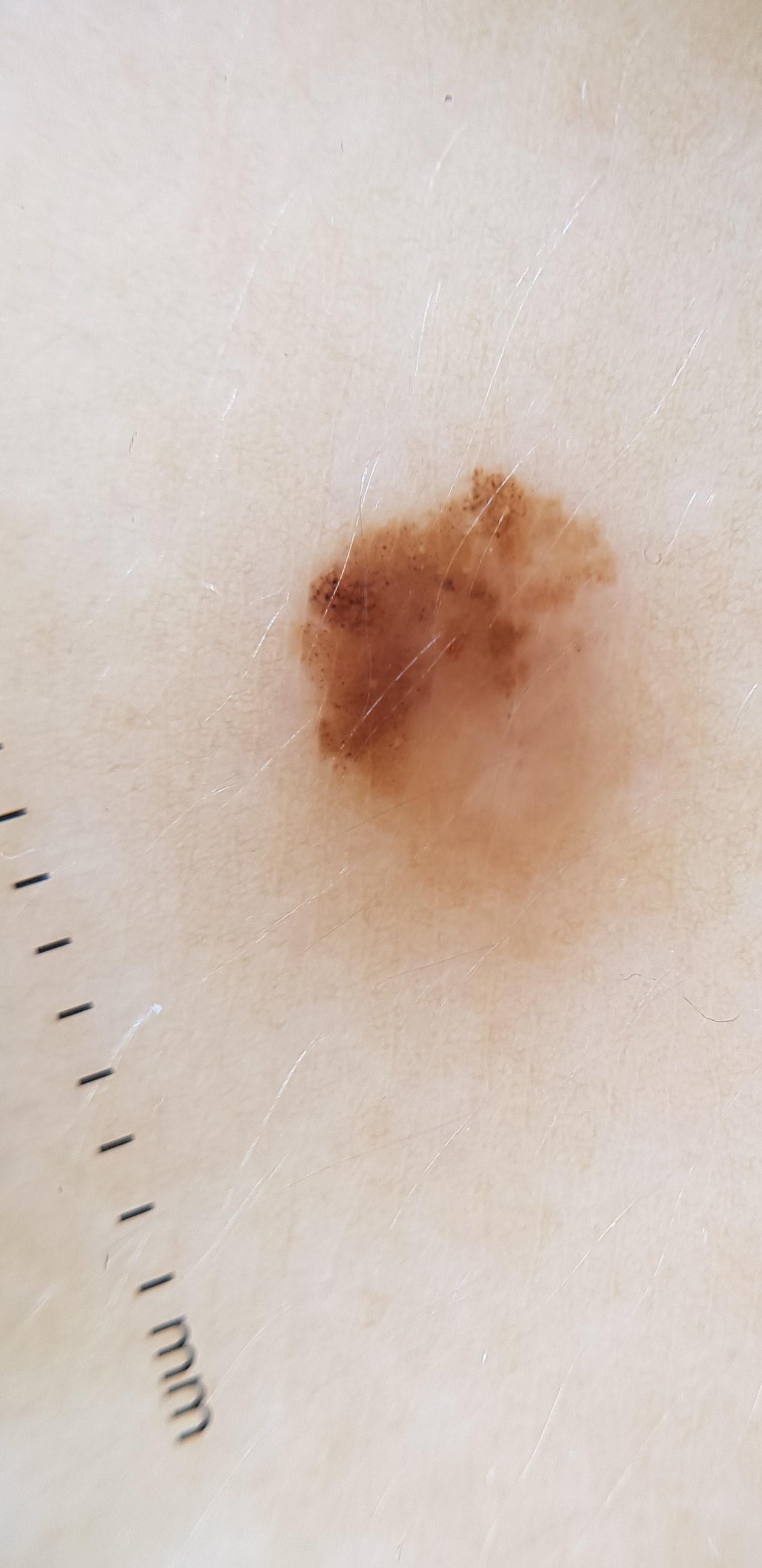Notes:
- subject: female, aged 28-32
- melanoma history: a prior melanoma
- Fitzpatrick: II
- image type: dermoscopy
- location: the trunk (the posterior trunk)
- diagnostic label: Melanoma (biopsy-proven)